Close-up view — 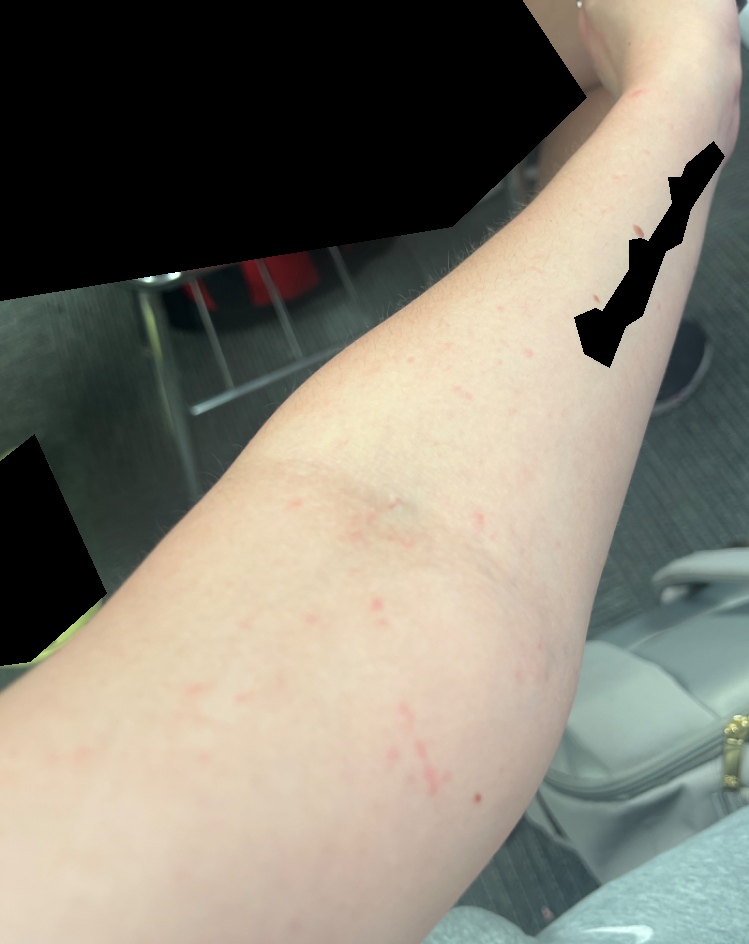The reviewer was unable to grade this case for skin condition.